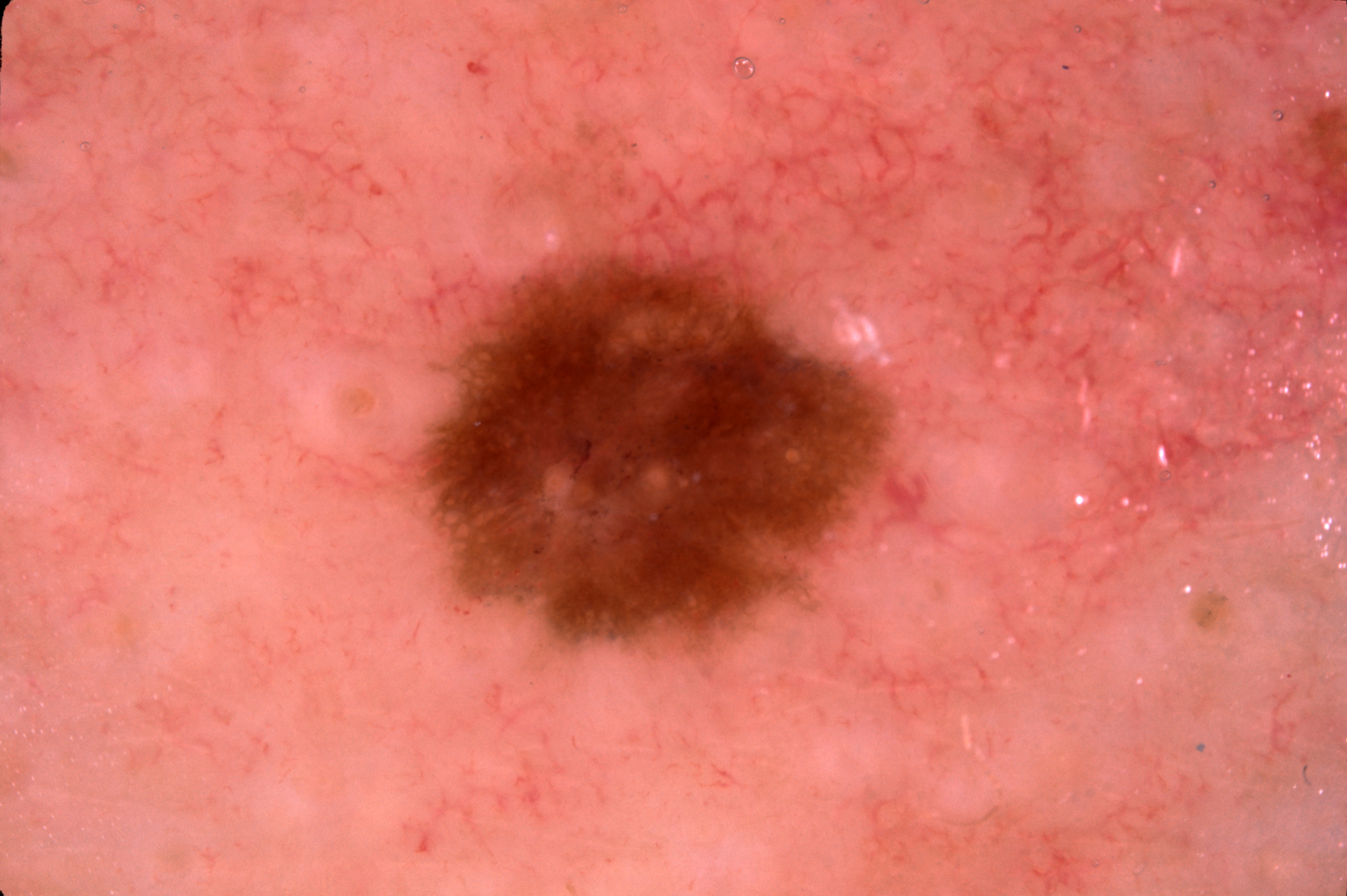A dermoscopic image of a skin lesion. The subject is a male approximately 55 years of age. A moderately sized lesion. Dermoscopy demonstrates pigment network; no milia-like cysts, streaks, or negative network. With coordinates (x1, y1, x2, y2), the lesion's extent is bbox(423, 255, 891, 646). The diagnostic assessment was a melanocytic nevus.